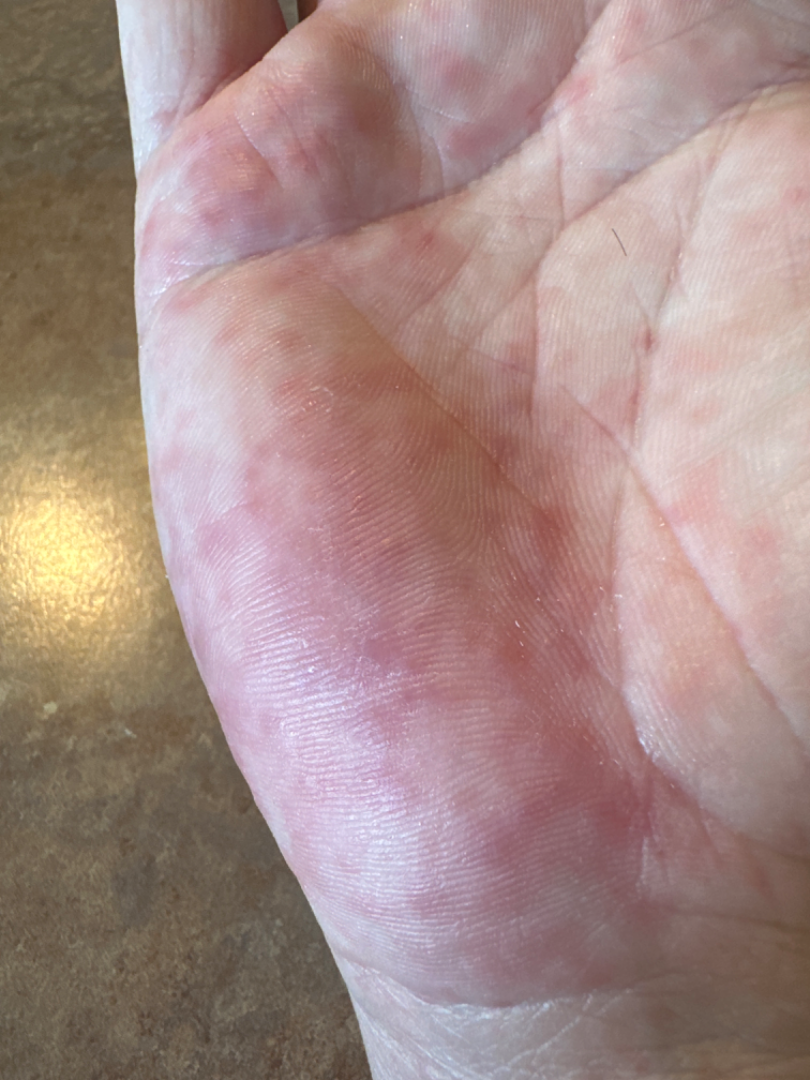The primary impression is Hand foot and mouth disease; also consider Viral Exanthem; a remote consideration is Urticaria.